The photograph was taken at a distance — 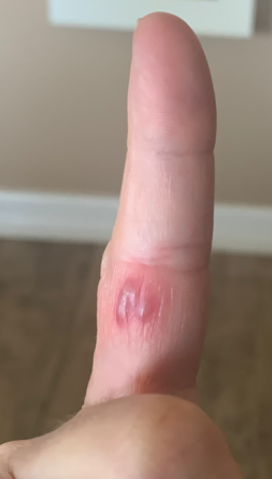lesion texture = raised or bumpy and fluid-filled
reported symptoms = itching and pain
duration = less than one week
patient's own categorization = a rash
skin tone = Fitzpatrick skin type II; lay graders estimated Monk skin tone scale 2
differential = most consistent with Herpes Simplex; possibly Insect Bite; an alternative is Eczema